A dermoscopic photograph of a skin lesion: 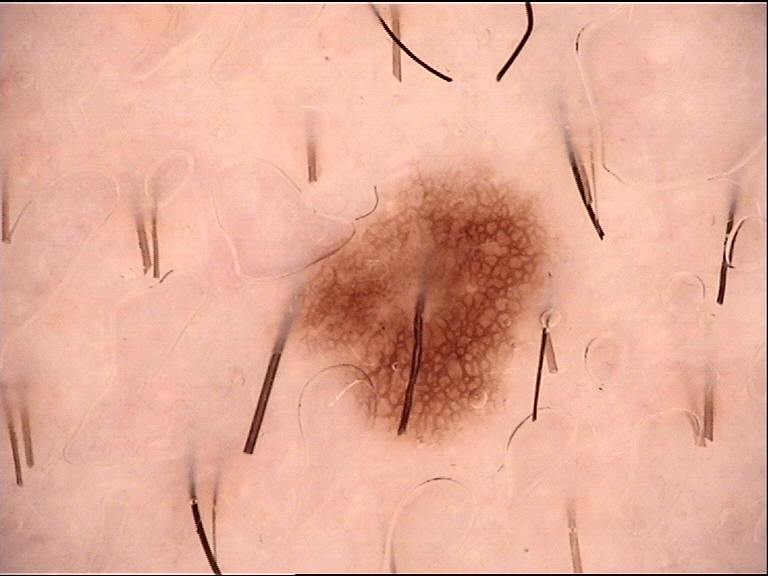Case:
* label: dysplastic junctional nevus (expert consensus)